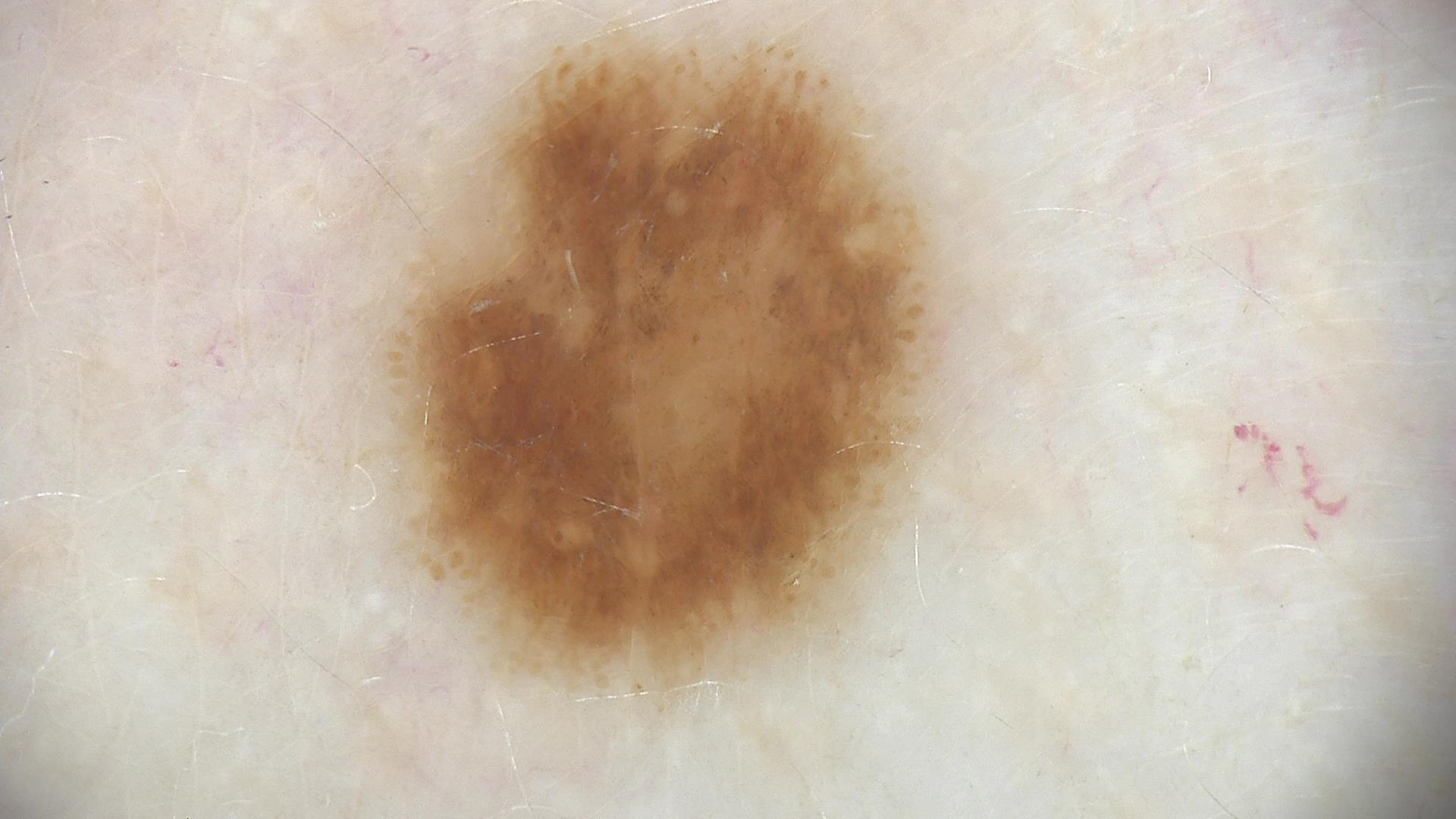The diagnosis was a dysplastic junctional nevus.